A dermoscopy image of a single skin lesion.
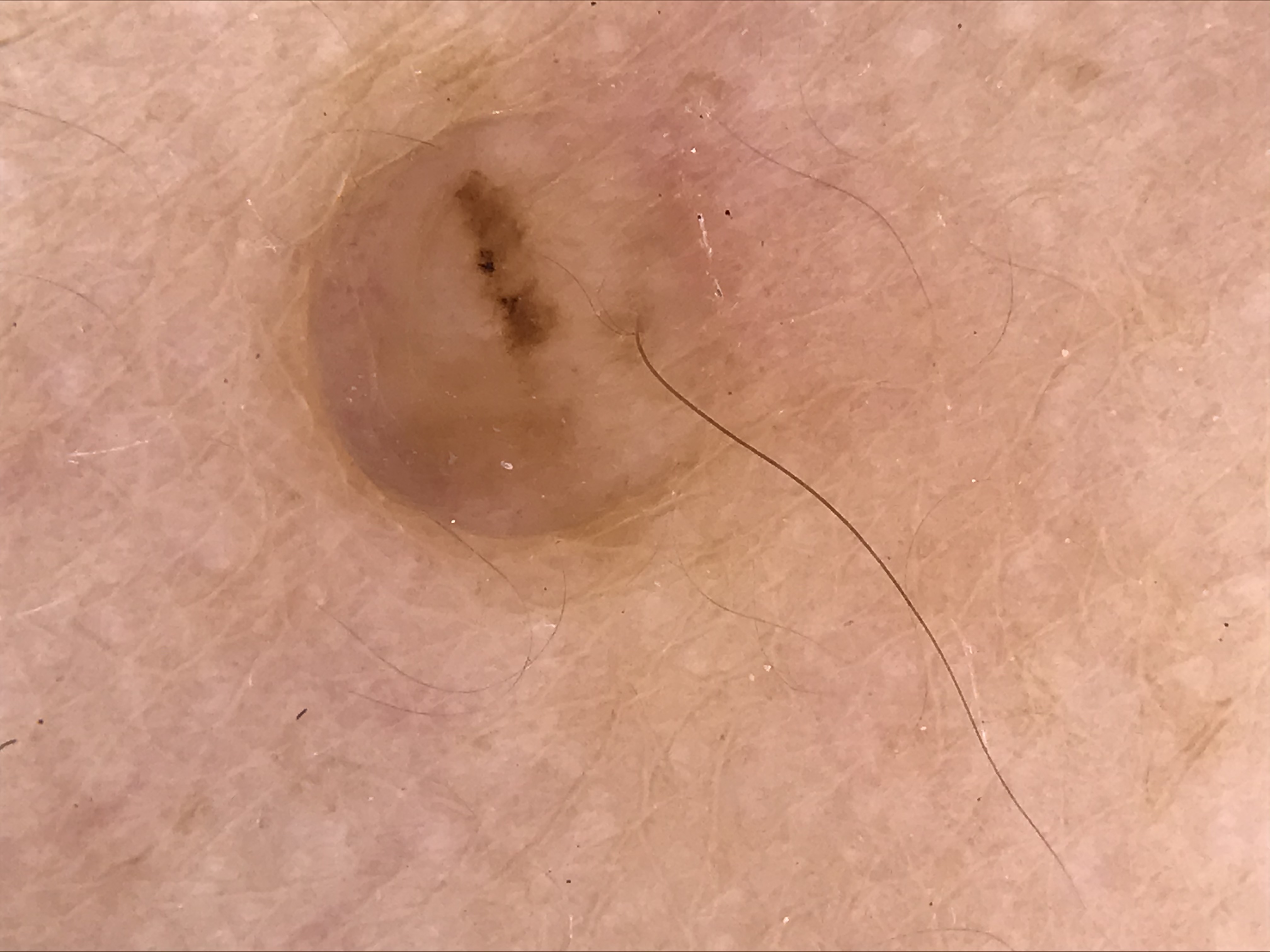Case:
This is a banal lesion.
Impression:
Diagnosed as a dermal nevus.